Few moles overall by the patient's own estimate · a male subject 79 years of age · the patient says their skin tans without first burning · a skin lesion imaged with a dermatoscope · imaged for a research study, with no referral diagnosis recorded:
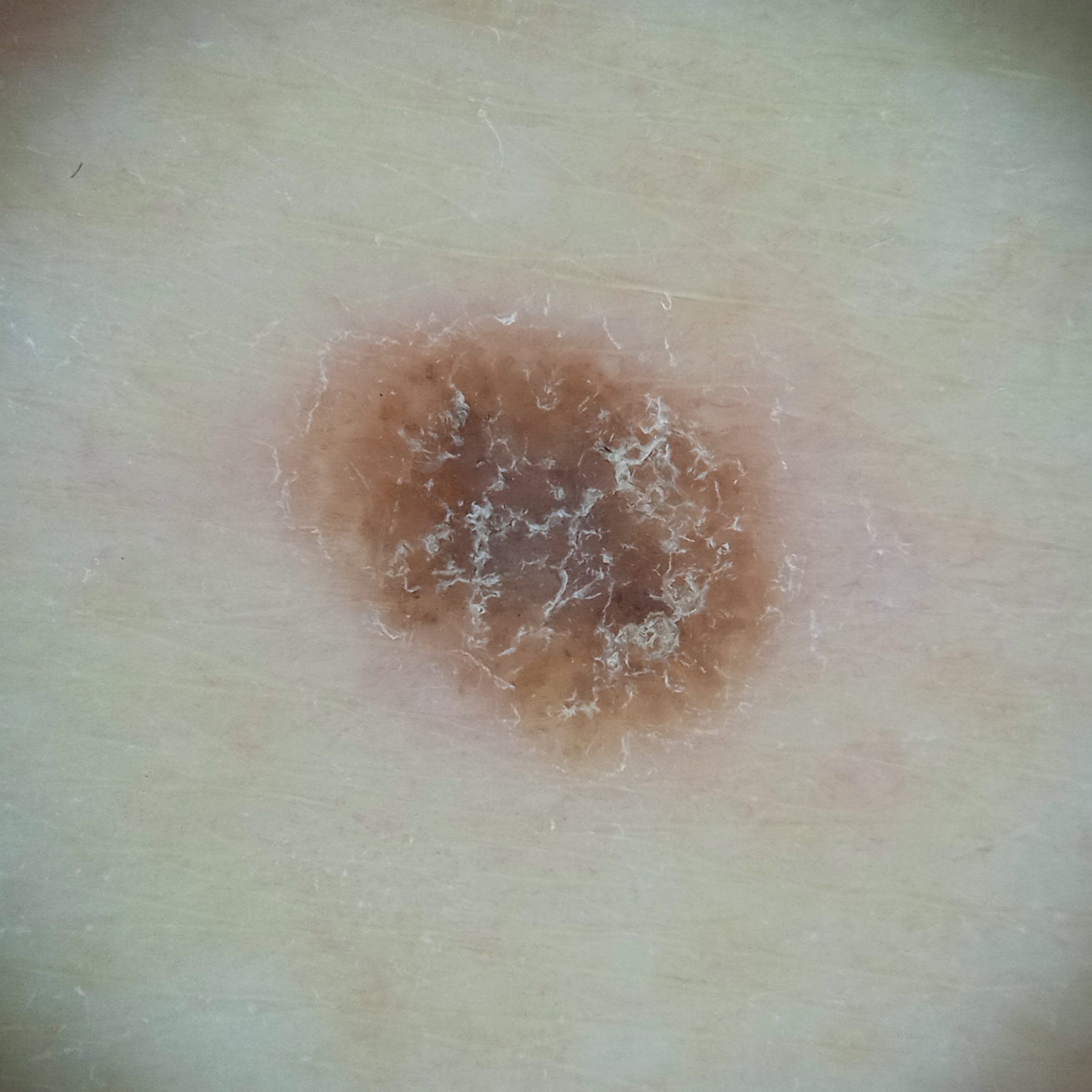Findings:
The lesion measures approximately 5.9 mm.
Assessment:
The four-dermatologist consensus diagnosis was a seborrheic keratosis; all four reviewers agreed; the reviewers were moderately confident; an alternative consideration was a melanocytic nevus.